Female contributor, age 60–69 · the contributor notes the lesion is rough or flaky · present for more than one year · no associated systemic symptoms reported · the contributor notes bleeding, enlargement, itching and bothersome appearance · located on the palm and sole of the foot · the photograph was taken at an angle:
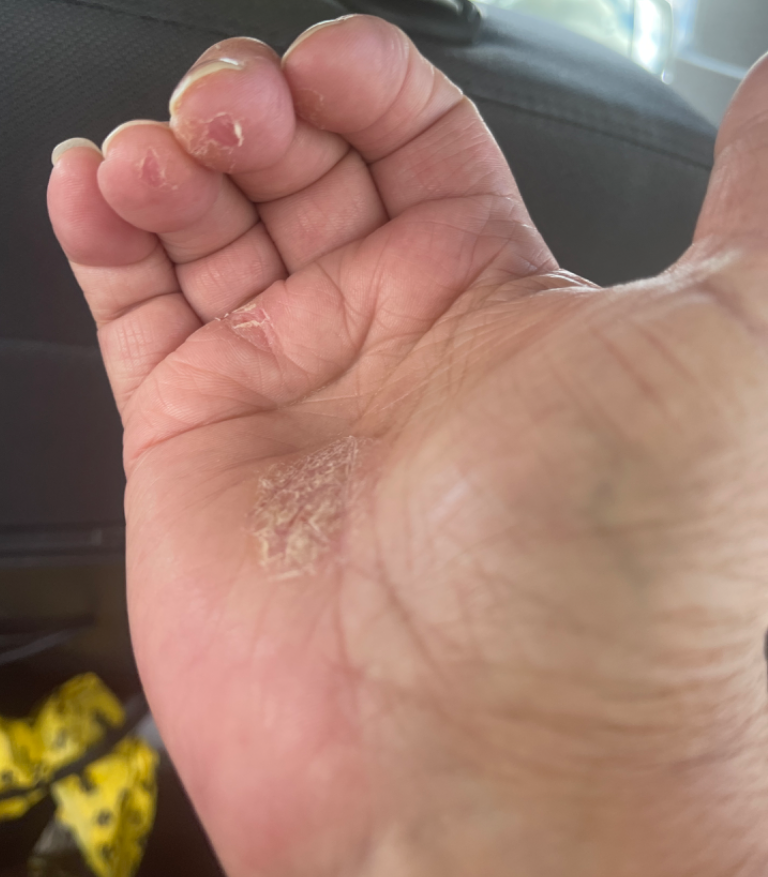Findings:
On remote review of the image, the leading impression is Psoriasis; also consider Eczema; a more distant consideration is Tinea.